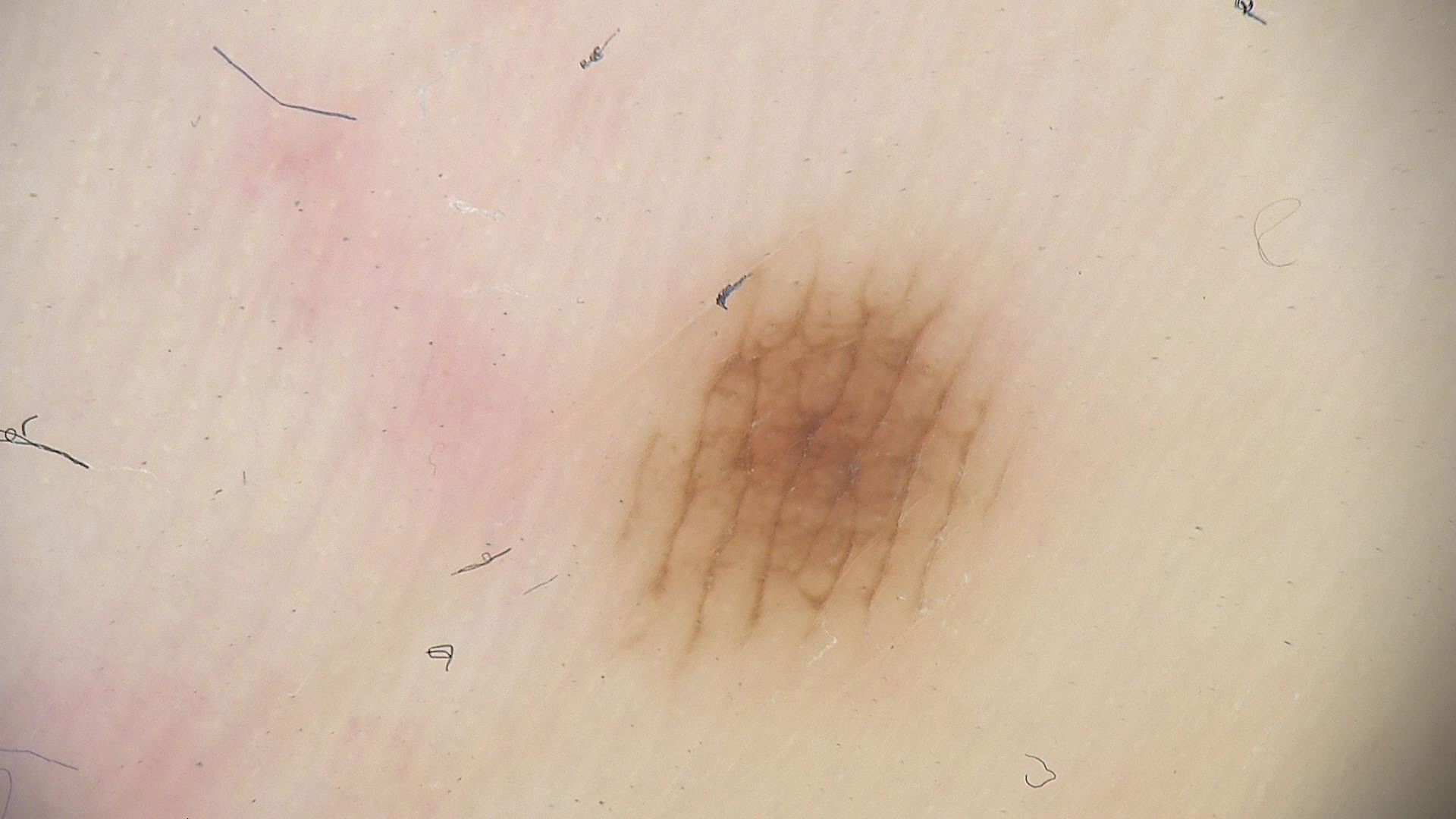class = acral dysplastic junctional nevus (expert consensus).